This is a close-up image.
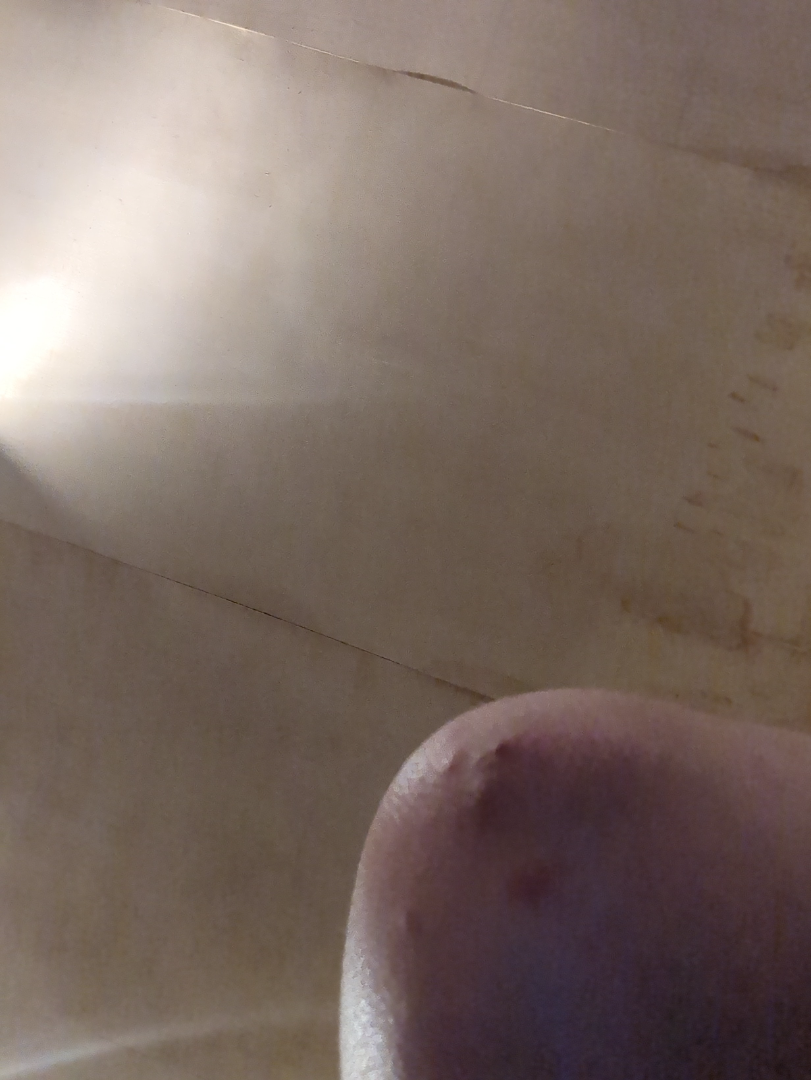The skin findings could not be characterized from the image.